Self-categorized by the patient as a rash · the lesion involves the front of the torso · the photo was captured at a distance · the contributor notes the condition has been present for one to four weeks · male contributor, age 70–79 · the contributor notes enlargement — 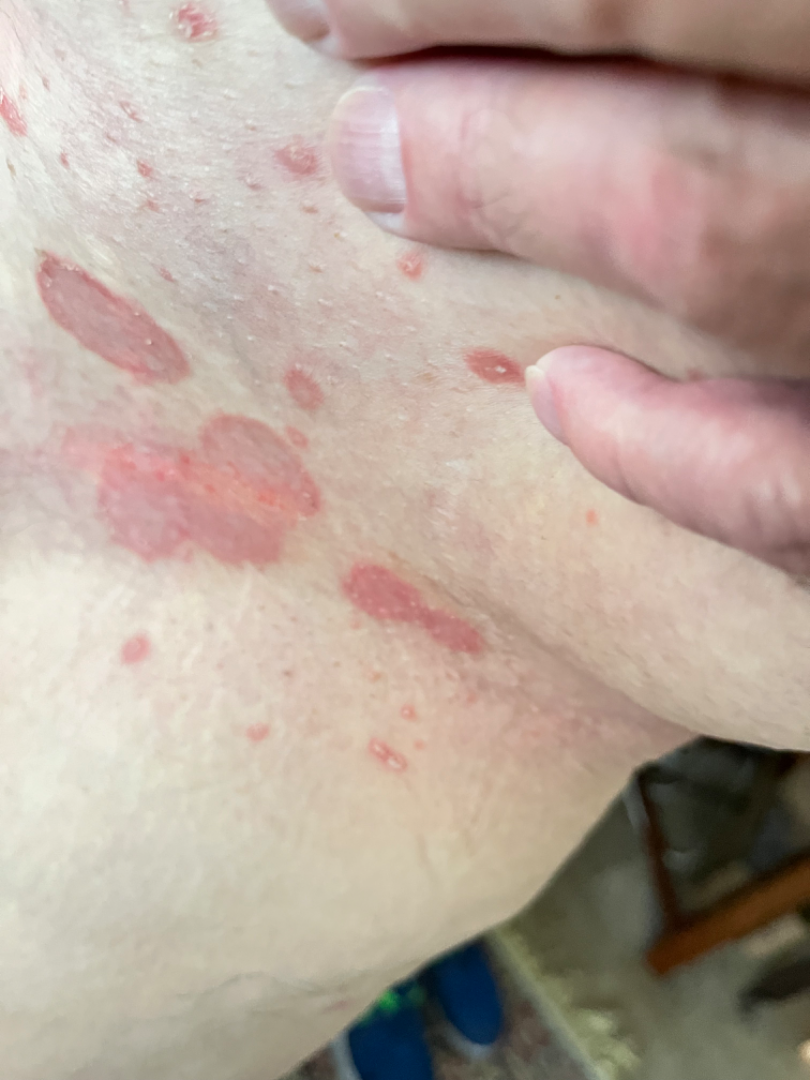On teledermatology review: the leading consideration is Inverse psoriasis; also raised was Candida; an alternative is Seborrheic Dermatitis.